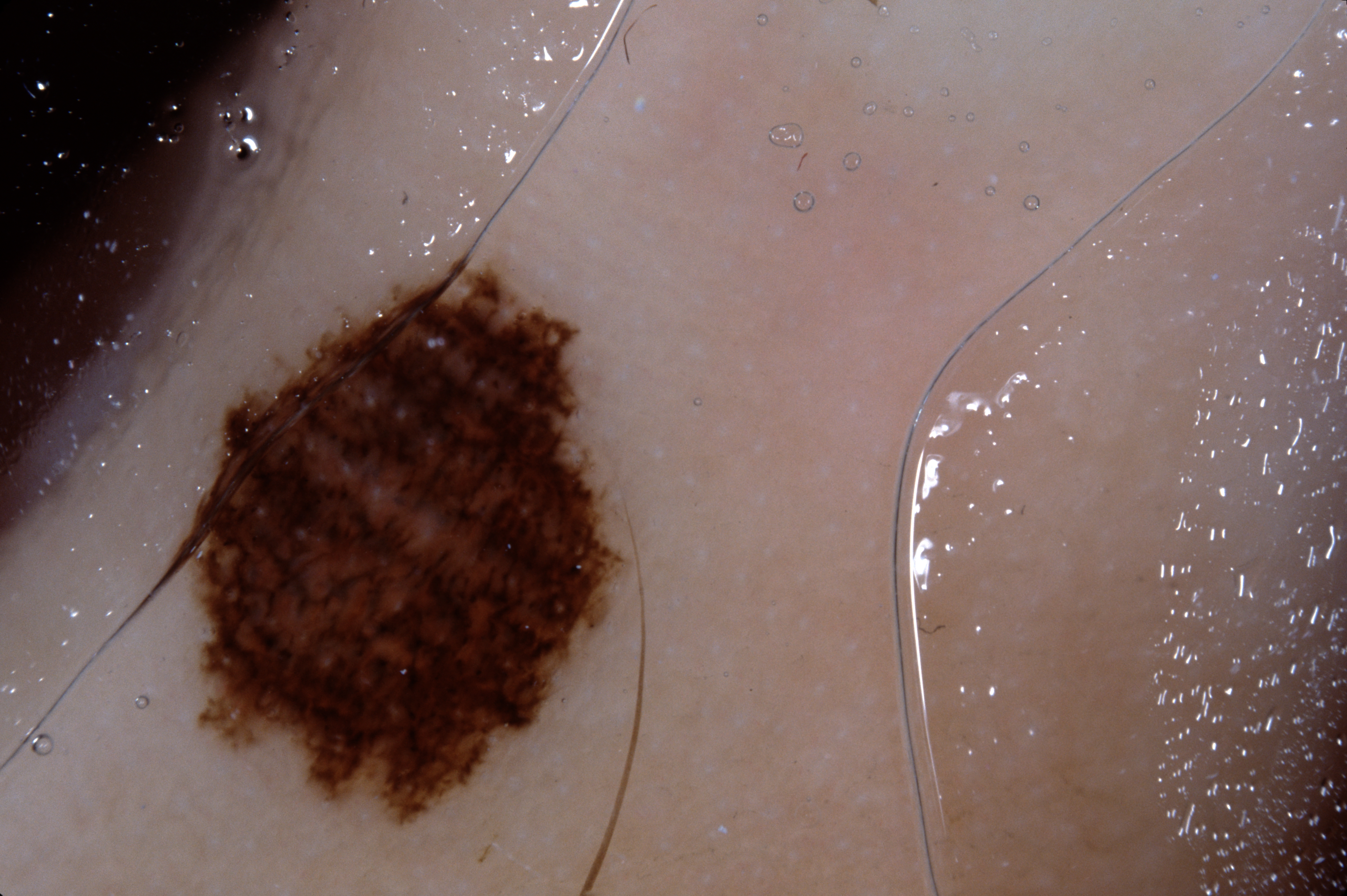A dermoscopic close-up of a skin lesion. A male patient, approximately 25 years of age. Dermoscopic assessment notes no milia-like cysts, negative network, pigment network, or streaks. In (x1, y1, x2, y2) order, the lesion is located at <bbox>117, 247, 632, 831</bbox>. A mid-sized lesion within the field. Consistent with a melanocytic nevus.